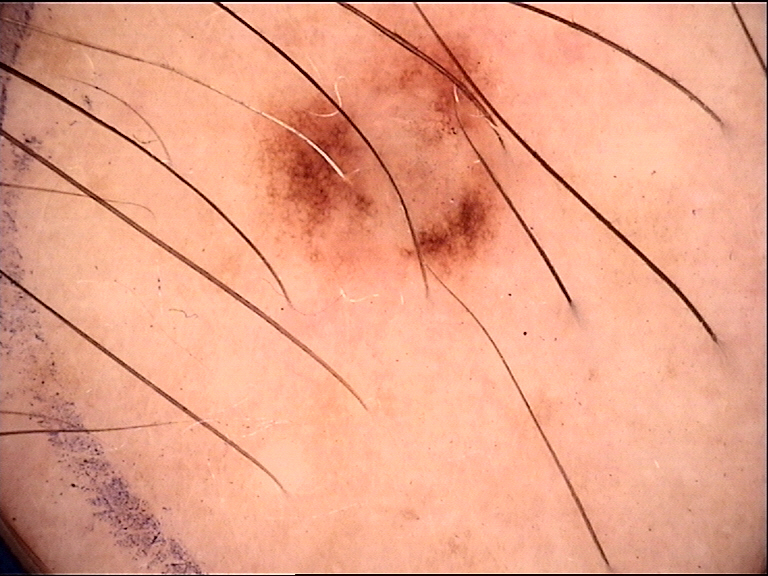Q: What is the imaging modality?
A: dermatoscopy
Q: What is this lesion?
A: dysplastic junctional nevus (expert consensus)